A dermoscopic image of a skin lesion:
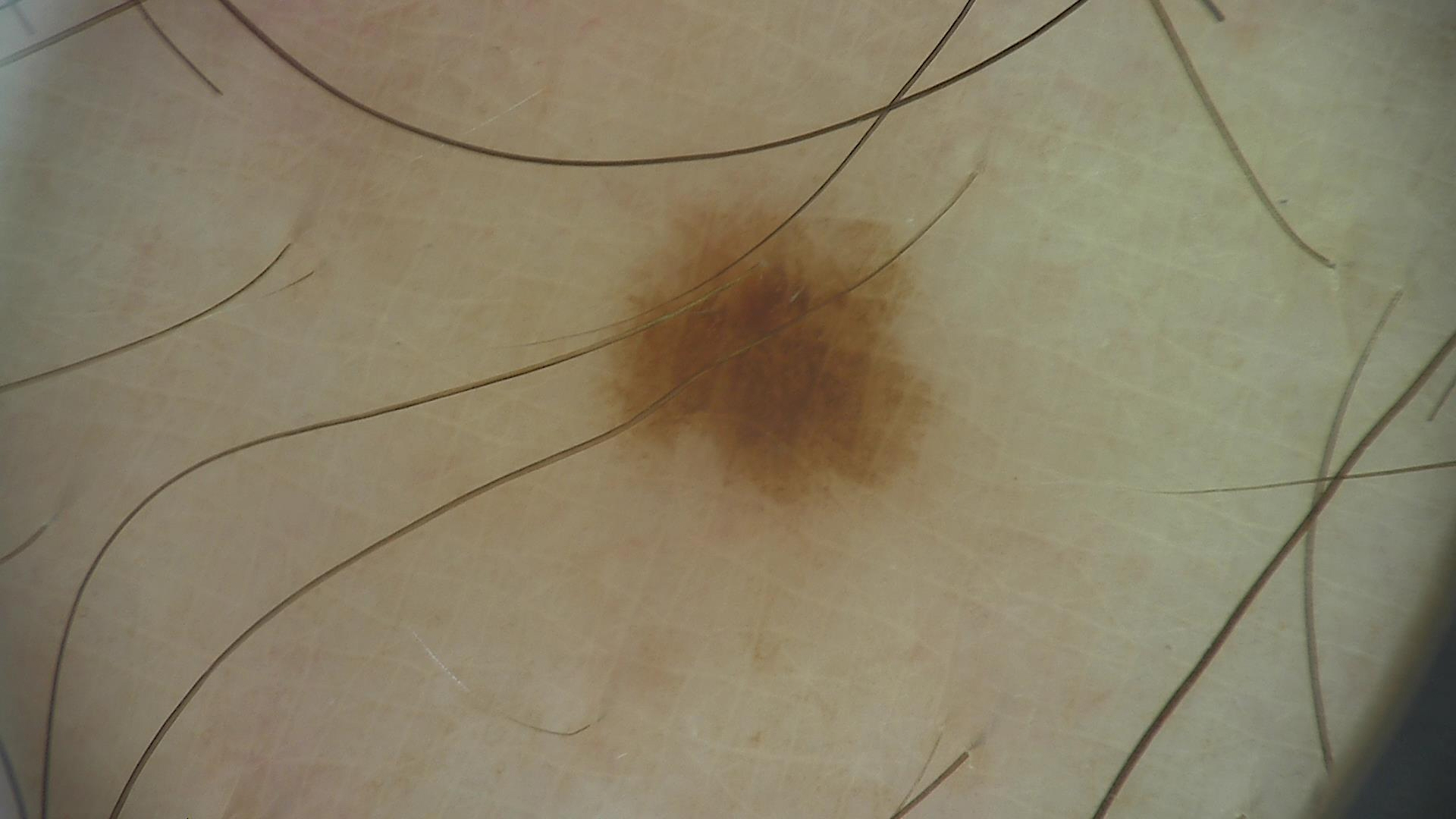lesion type = banal | label = junctional nevus (expert consensus).